Skin tone: Fitzpatrick II; the patient considered this a rash; the patient notes the condition has been present for less than one week; the palm, back of the hand and top or side of the foot are involved; the patient notes associated fever; a close-up photograph; texture is reported as raised or bumpy: 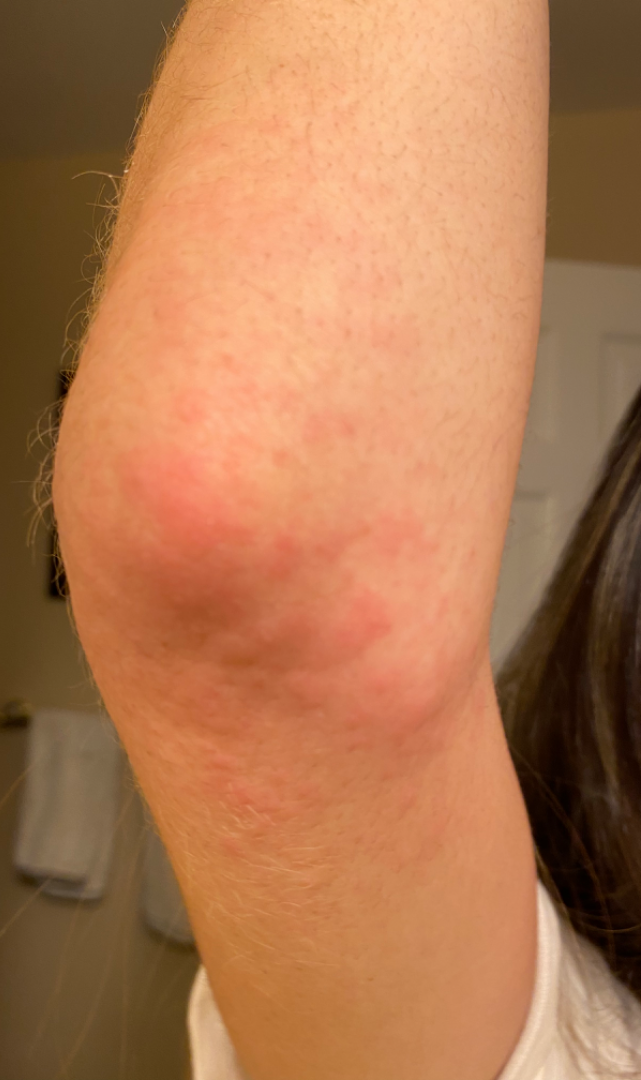Impression:
The skin condition could not be confidently assessed from this image.